Collected as part of a research study, without a referral diagnosis; a dermoscopy image of a skin lesion; the patient says their skin reddens painfully with sun exposure; the patient describes having a moderate number of moles; a female patient age 81.
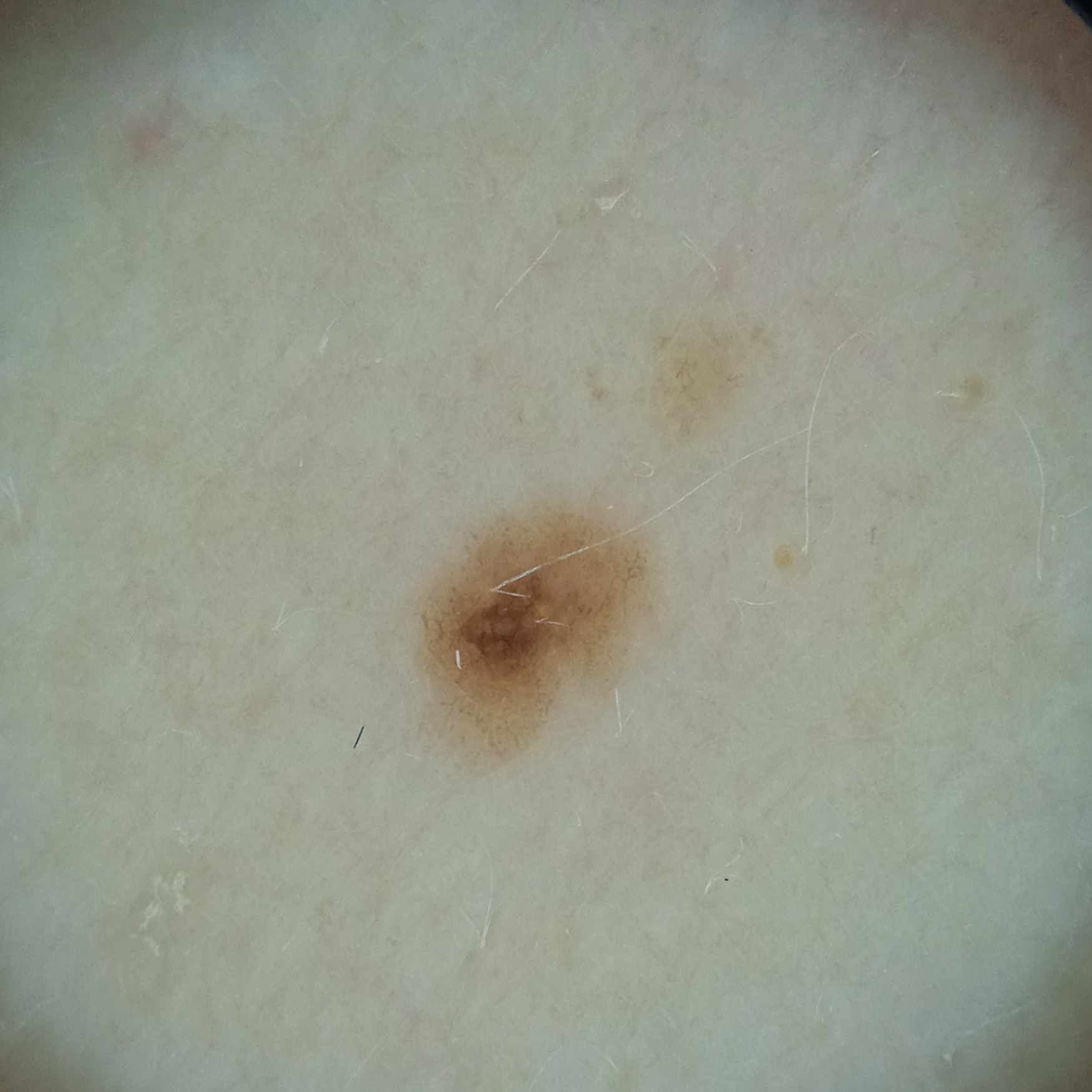Summary:
The lesion involves the back. Measuring roughly 2.7 mm.
Assessment:
The diagnostic impression was a melanocytic nevus.